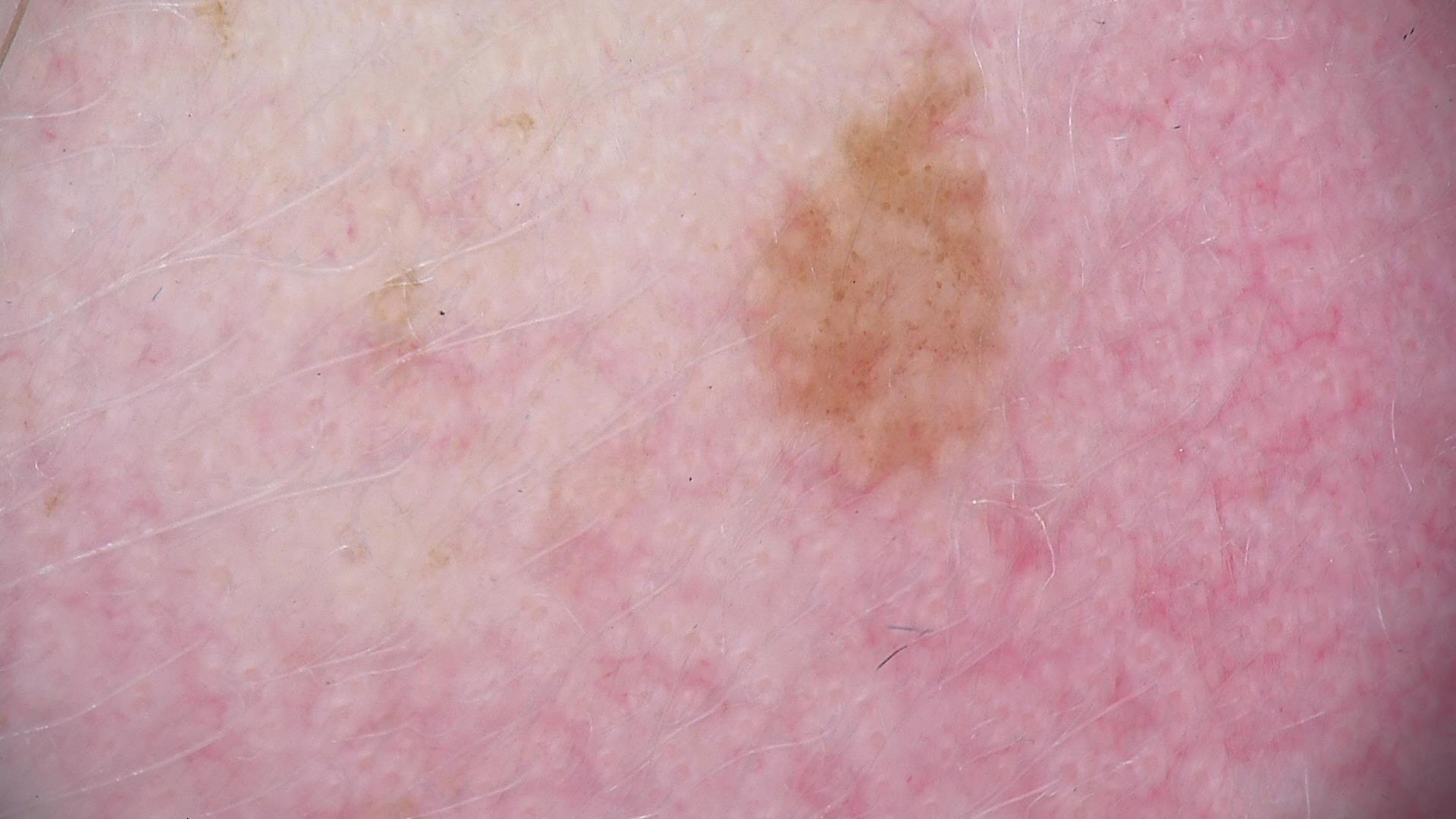Summary: A dermoscopic close-up of a skin lesion. Impression: Classified as a dysplastic junctional nevus.